A male patient aged approximately 75. The patient is Fitzpatrick phototype I — 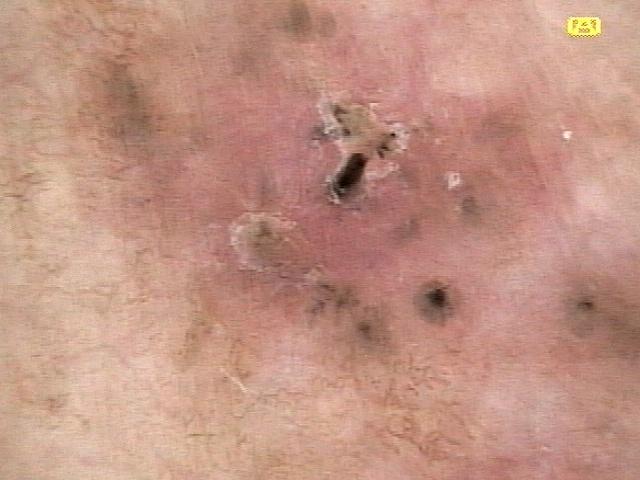site — the trunk (the anterior trunk); diagnostic label — Basal cell carcinoma (biopsy-proven).